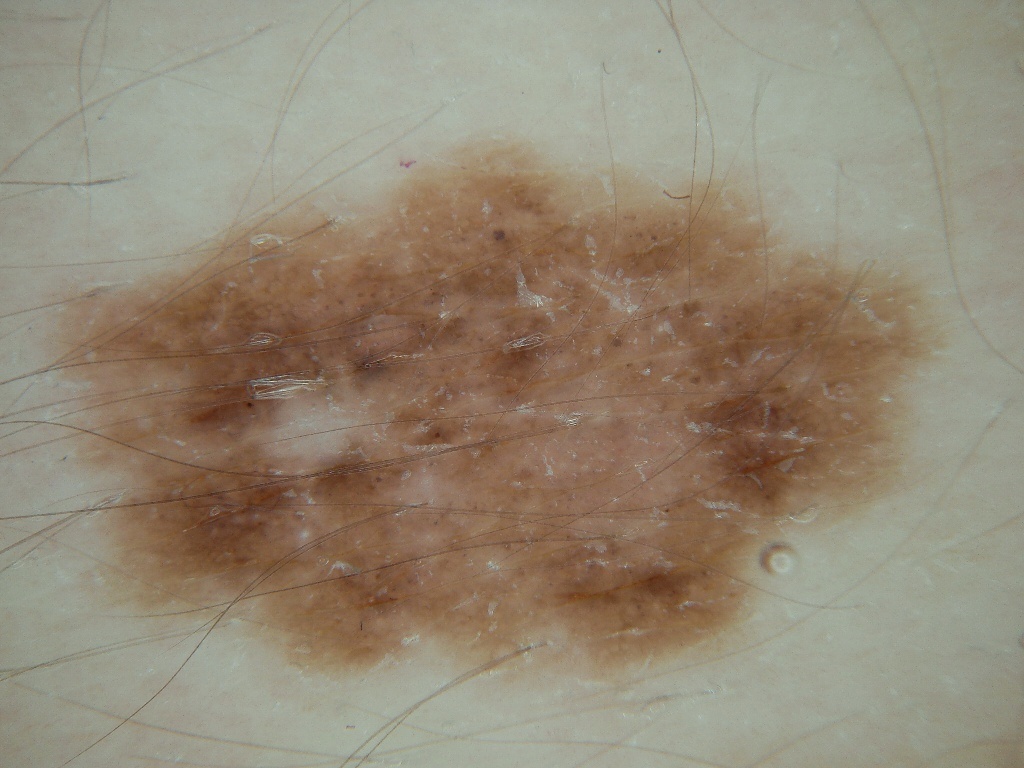Q: What is the imaging modality?
A: dermoscopy
Q: What is the lesion's bounding box?
A: 49 154 939 672
Q: Which assessed dermoscopic features were absent?
A: streaks and globules
Q: What is the diagnosis?
A: a benign lesion